Reported duration is less than one week. The patient considered this a rash. The patient indicates the lesion is raised or bumpy and fluid-filled. This image was taken at an angle. The lesion is associated with itching, pain and bothersome appearance. Located on the arm. No constitutional symptoms were reported. Female subject, age 40–49:
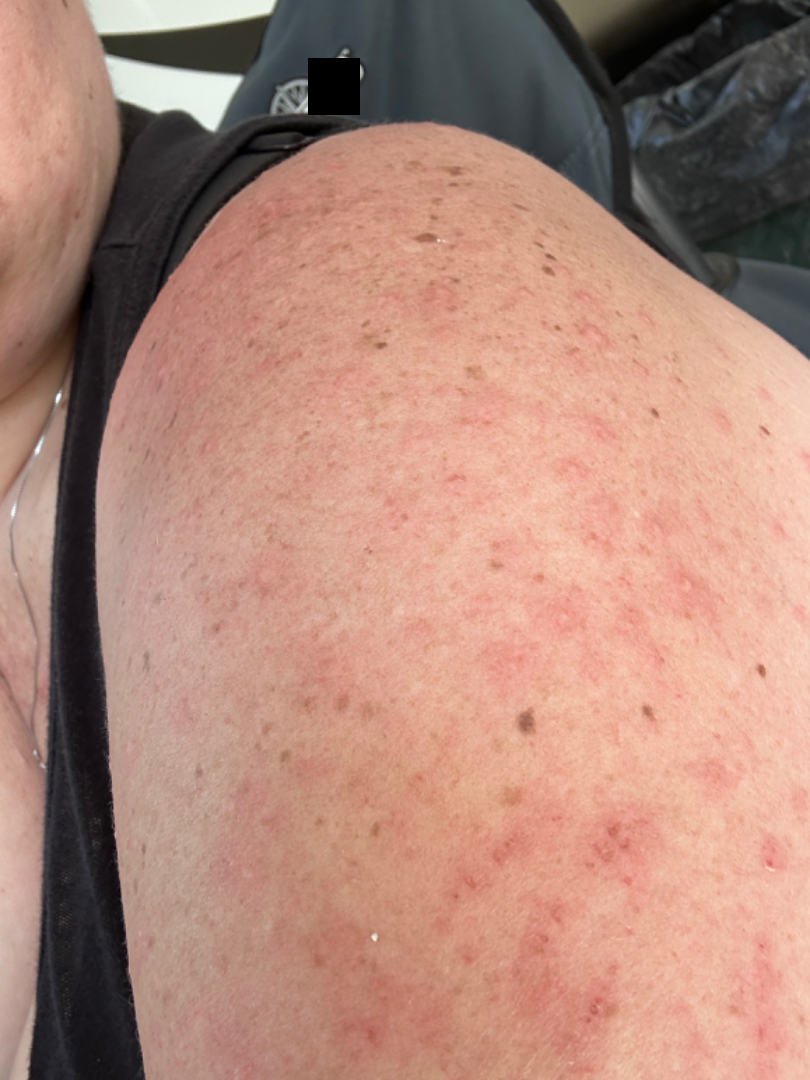Case summary:
* dermatologist impression — three dermatologists independently reviewed the case: favoring Acute dermatitis, NOS; a more distant consideration is Scabies; less probable is Folliculitis; less likely is Herpes Zoster; lower on the differential is Drug Rash; a remote consideration is Eczema; a more distant consideration is Allergic Contact Dermatitis